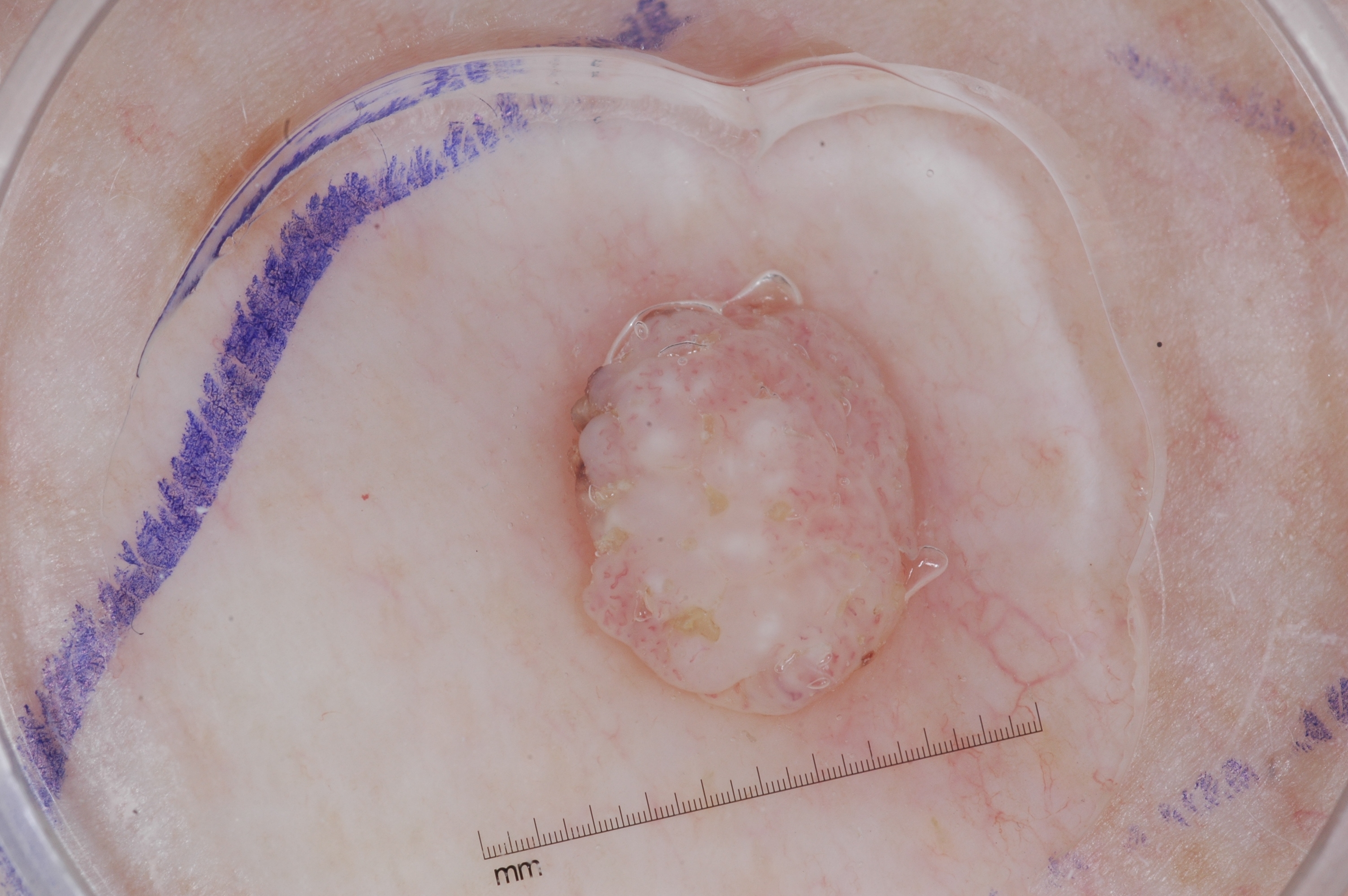modality: dermoscopy; subject: male, aged approximately 45; dermoscopic features: milia-like cysts; bounding box: <bbox>530, 249, 962, 734</bbox>; impression: a seborrheic keratosis, a benign lesion.